Dermoscopy of a skin lesion:
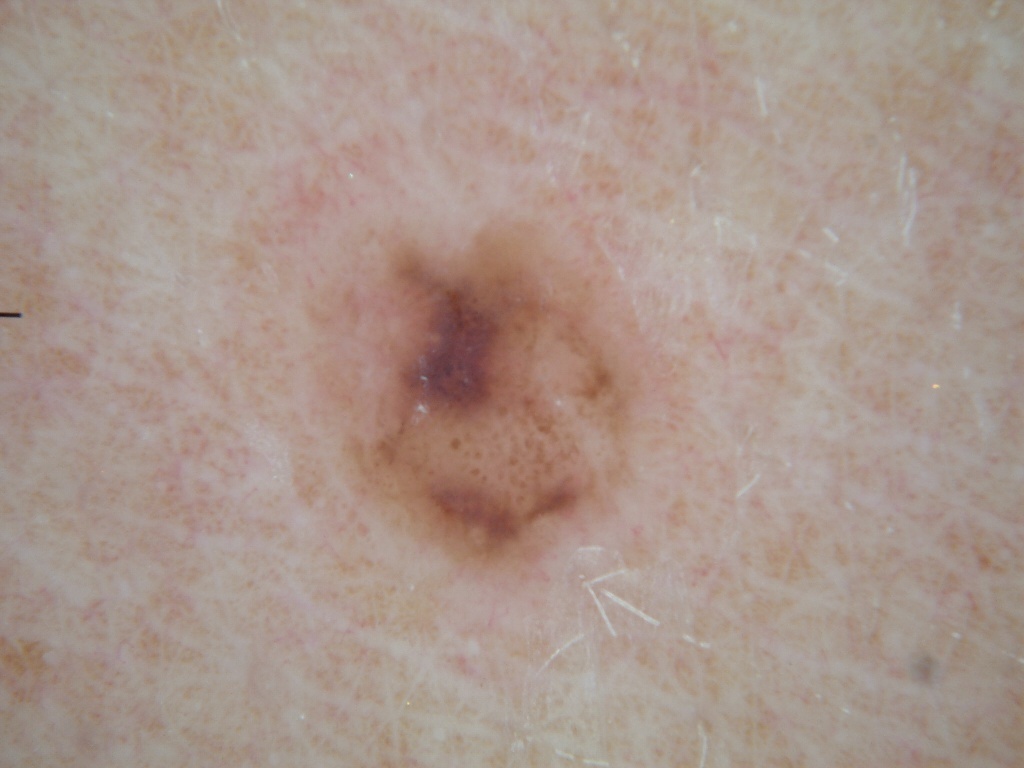| feature | finding |
|---|---|
| location | bbox=[305, 218, 675, 586] |
| diagnostic label | a melanocytic nevus |